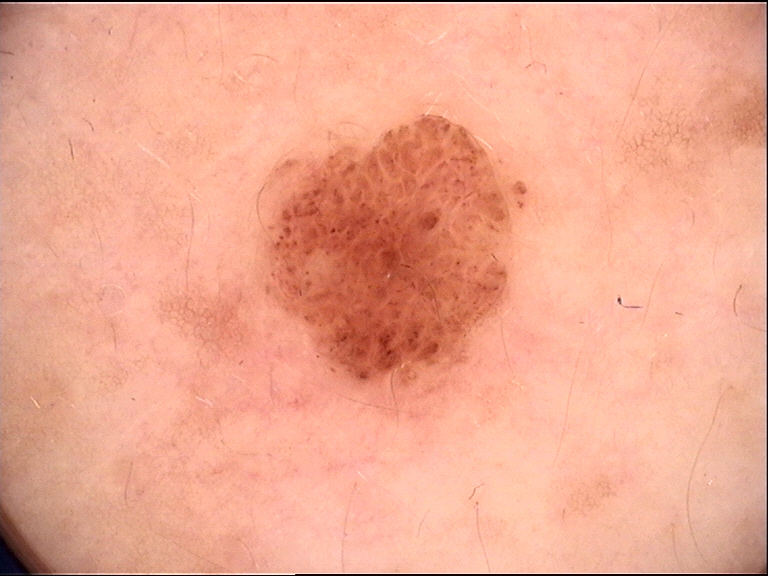A dermoscopy image of a single skin lesion.
The diagnosis was a compound nevus.